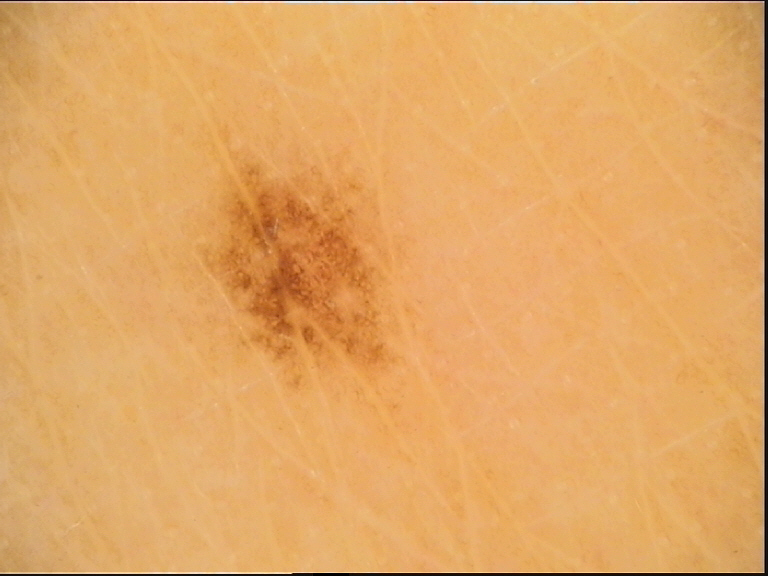A dermoscopic close-up of a skin lesion.
The diagnosis was a benign lesion — a dysplastic junctional nevus.